A skin lesion imaged with a dermatoscope.
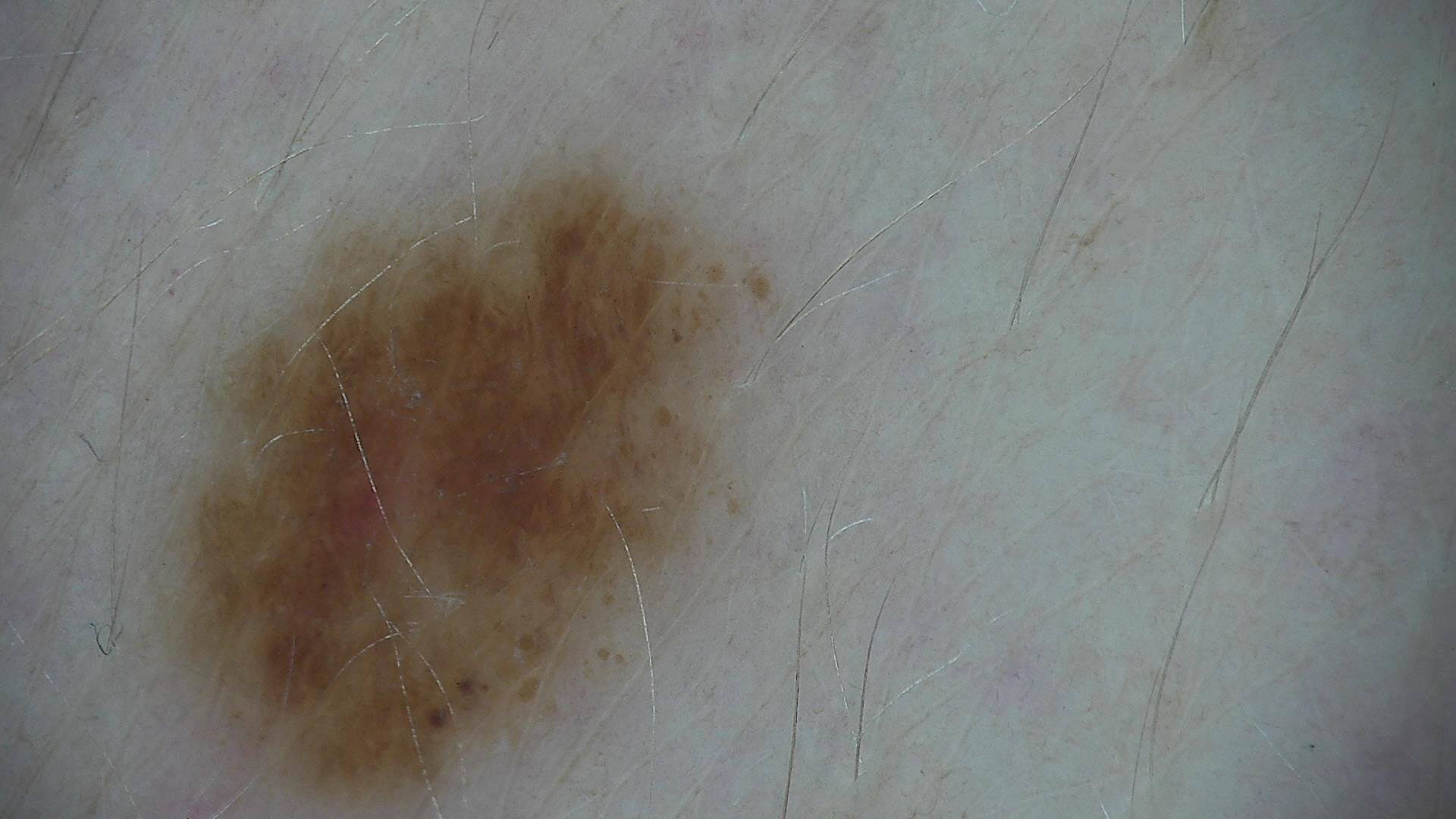Conclusion: The diagnosis was a dysplastic junctional nevus.